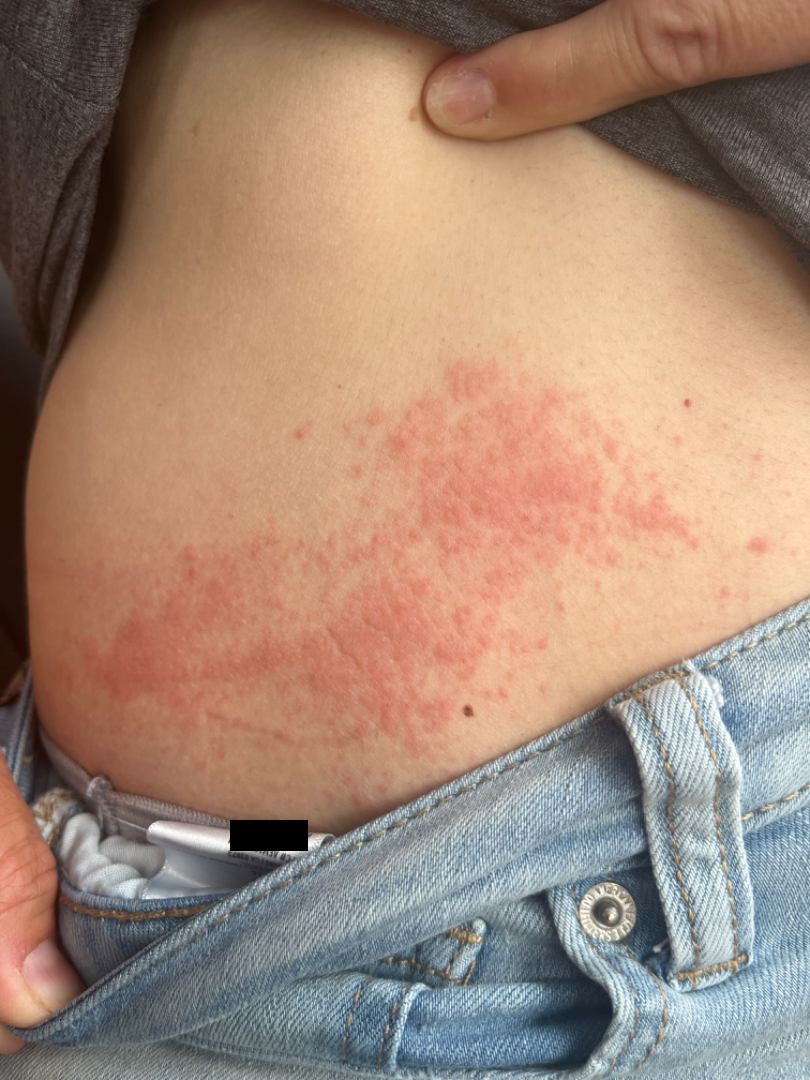A close-up photograph. On photographic review by a dermatologist: Allergic Contact Dermatitis (1.00).